A dermatoscopic image of a skin lesion; a male subject about 80 years old: 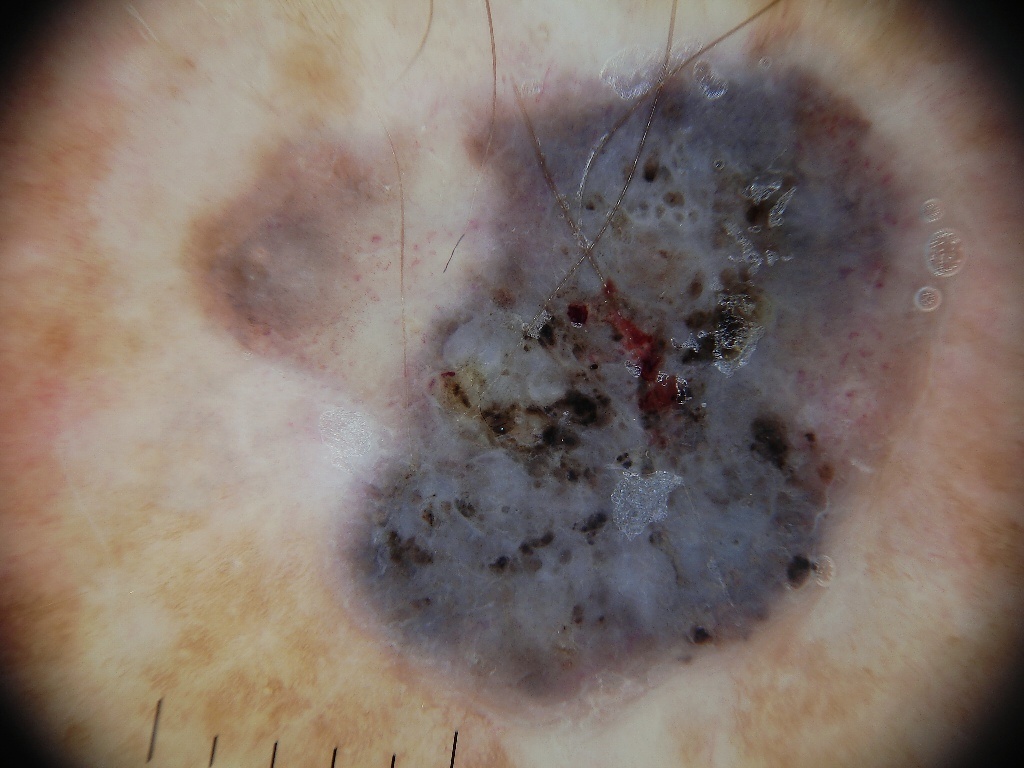location: x1=172, y1=29, x2=967, y2=760; features: negative network and globules; impression: a melanoma.